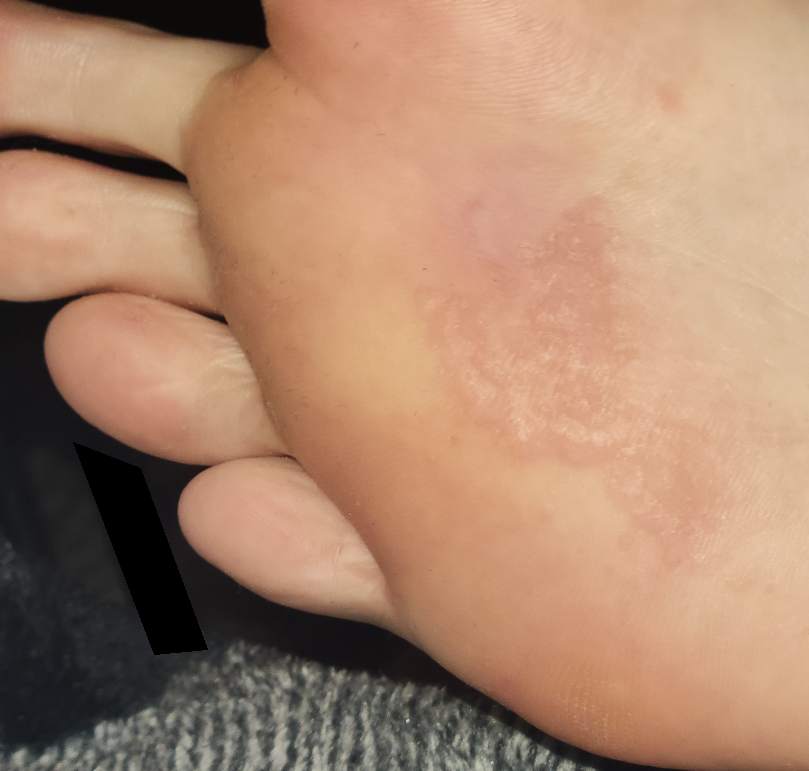assessment = unable to determine.